Dermoscopy of a skin lesion:
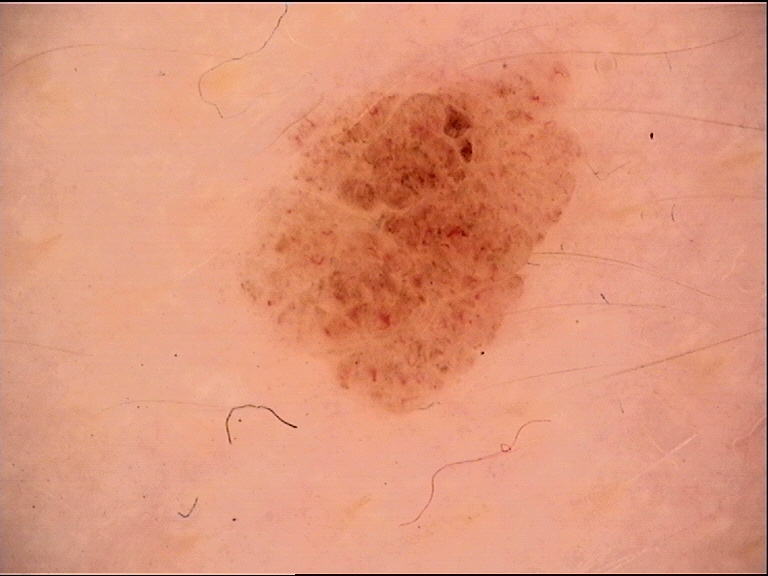The diagnostic label was a banal lesion — a compound nevus.